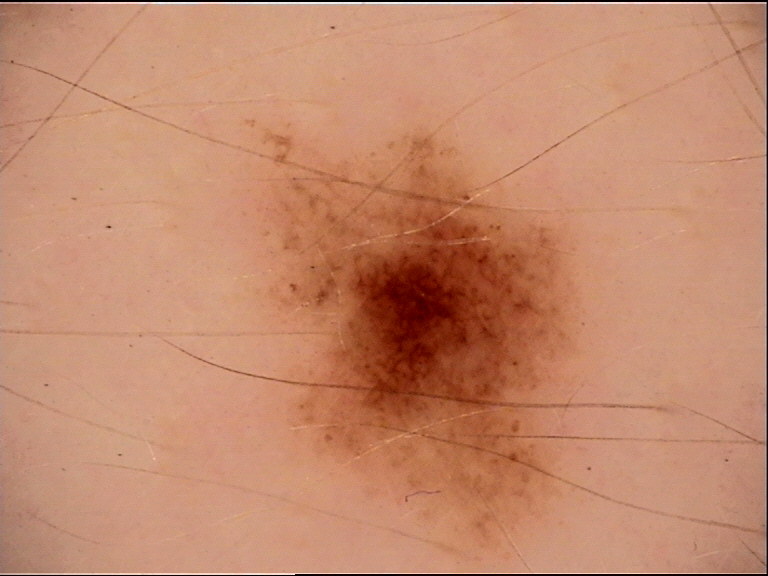Diagnosed as a dysplastic junctional nevus.